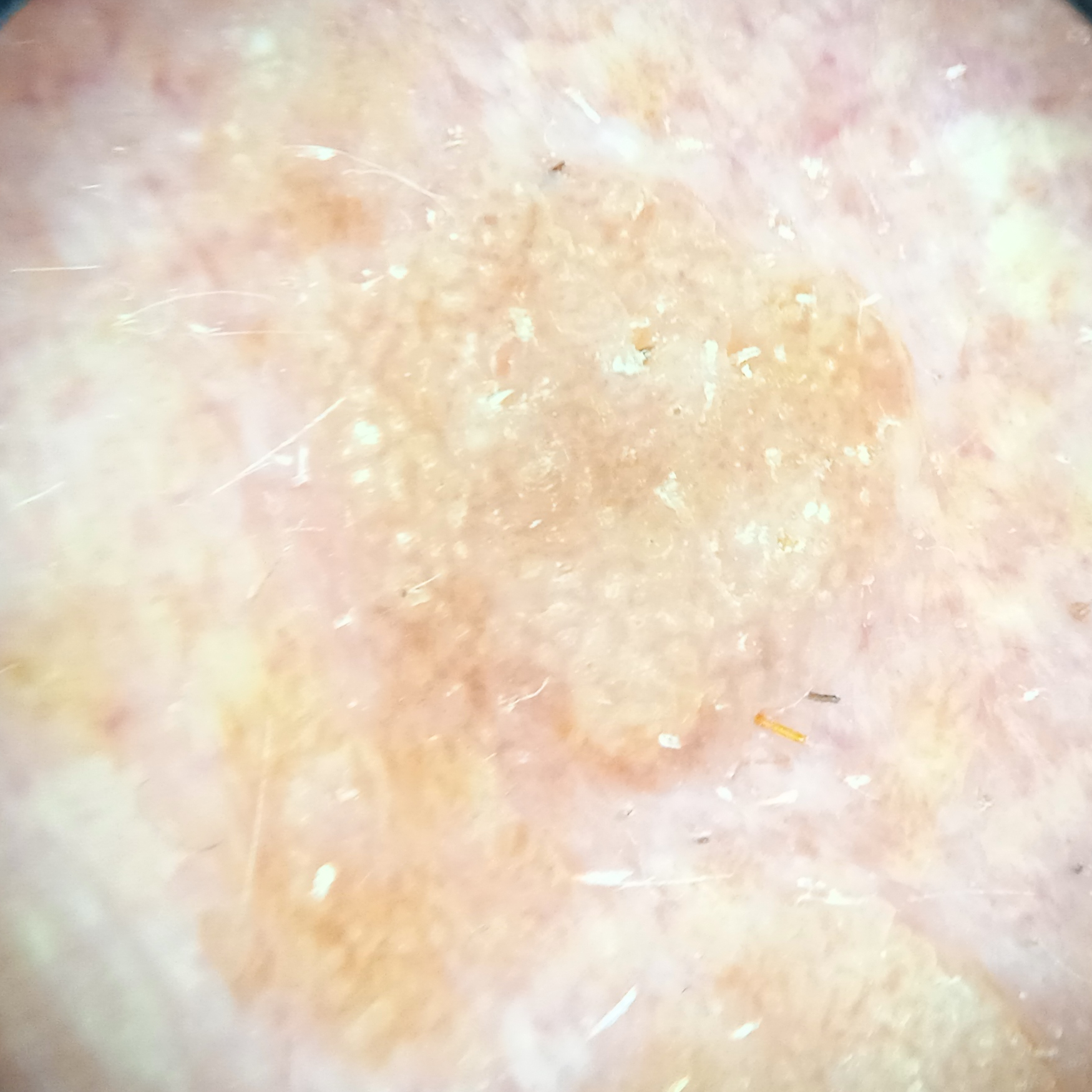The patient reports no prior organ transplant.
A male patient 62 years of age.
The patient says their skin reddens with sun exposure.
The lesion was assessed as a seborrheic keratosis.